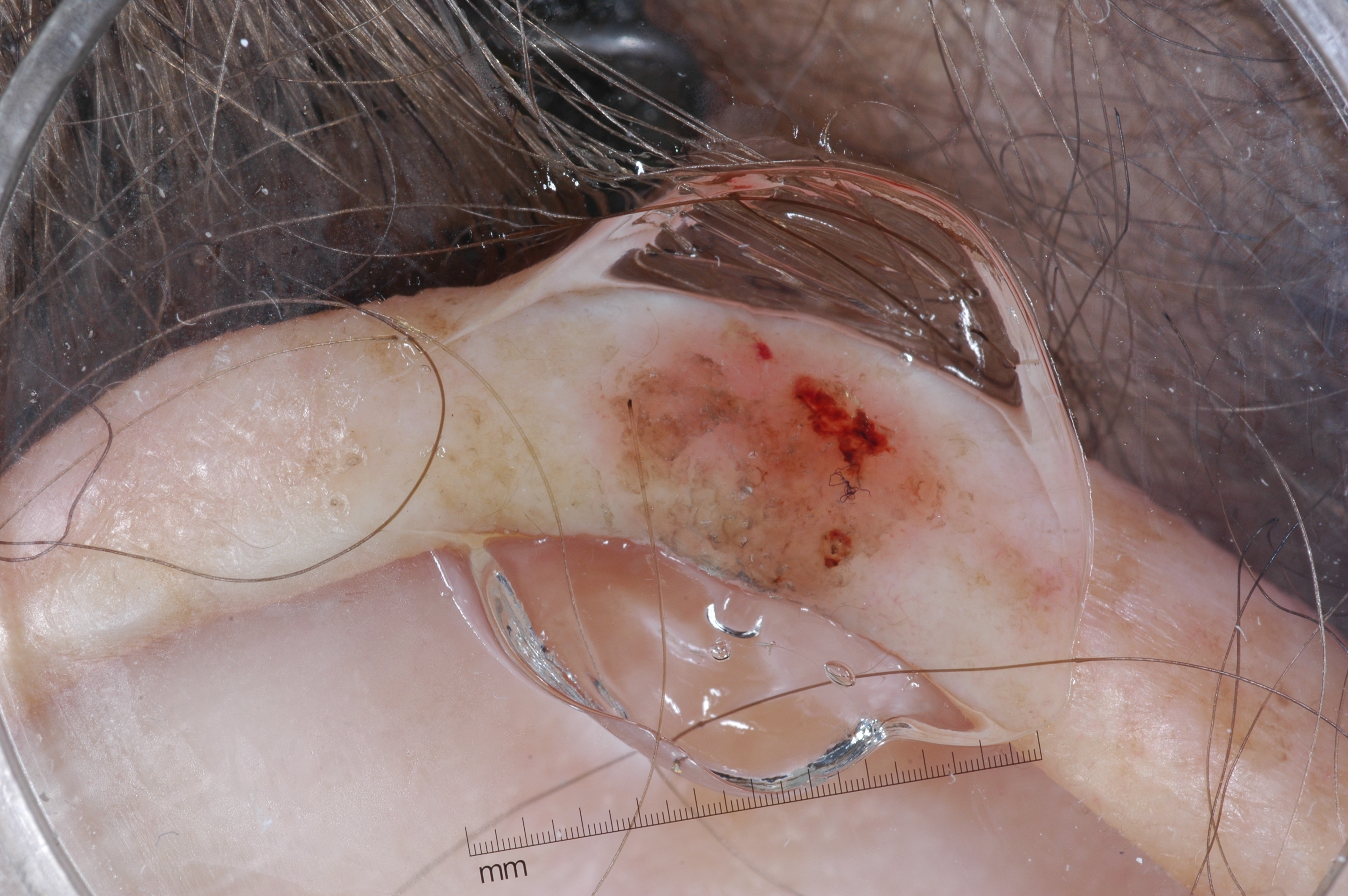  image:
    modality: dermoscopy
  lesion_location:
    bbox_xyxy:
      - 589
      - 303
      - 974
      - 608
  dermoscopic_features:
    present: []
    absent:
      - milia-like cysts
      - streaks
      - negative network
      - pigment network
  lesion_extent:
    approx_field_fraction_pct: 8
  diagnosis:
    name: seborrheic keratosis
    malignancy: benign
    lineage: keratinocytic
    provenance: clinical